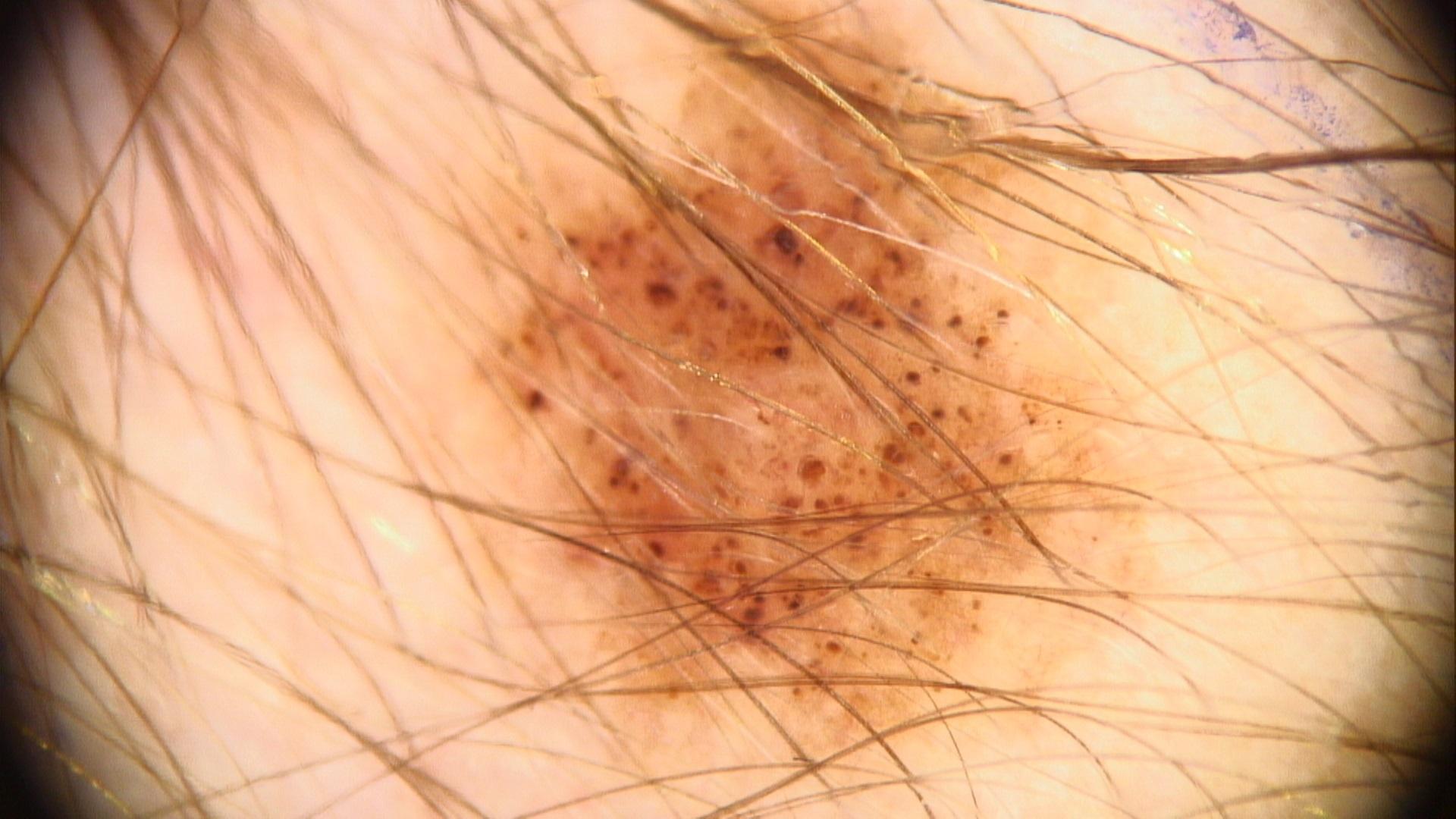Clinical context:
A female patient about 30 years old. A dermoscopy image of a single skin lesion. The lesion is on the trunk.
Assessment:
The clinical impression was a nevus.